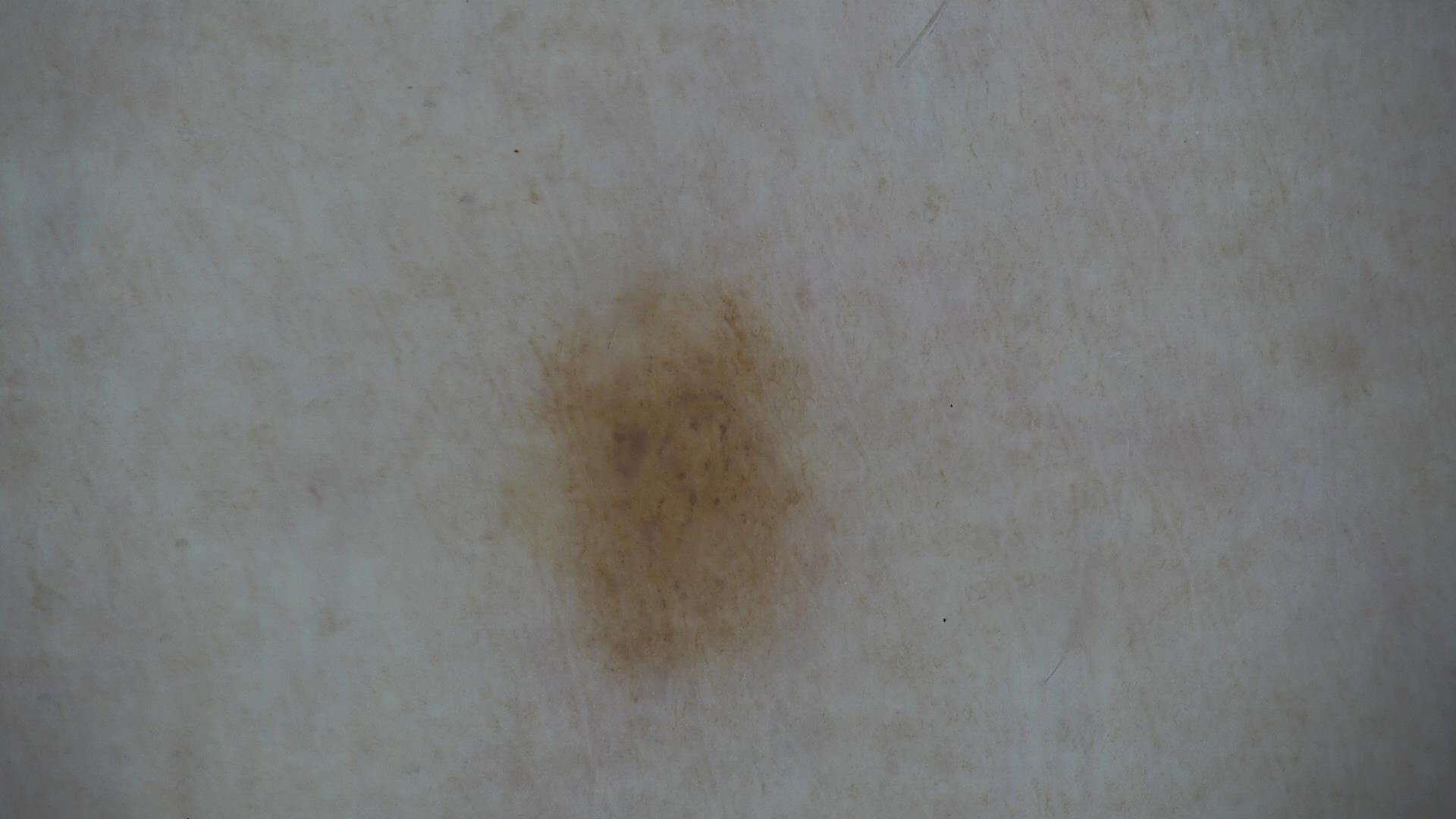  image: dermatoscopy
  diagnosis:
    name: dysplastic junctional nevus
    code: jd
    malignancy: benign
    super_class: melanocytic
    confirmation: expert consensus